The patient is a female aged 40–49, the lesion involves the leg, the photograph is a close-up of the affected area.
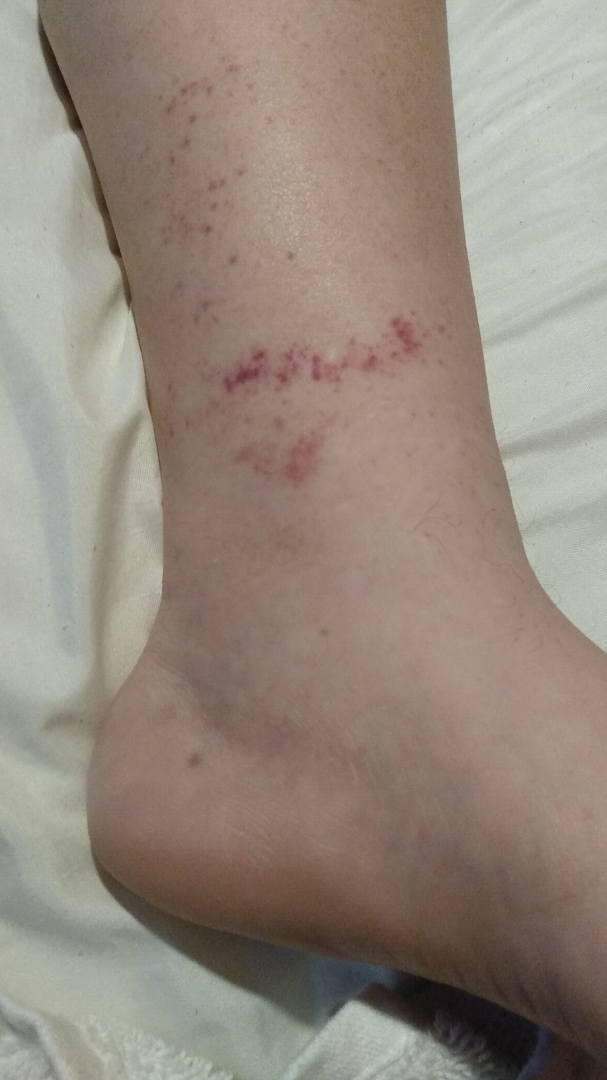{
  "differential": {
    "tied_lead": [
      "Pigmented purpuric eruption",
      "Vasculitis of the skin"
    ]
  }
}